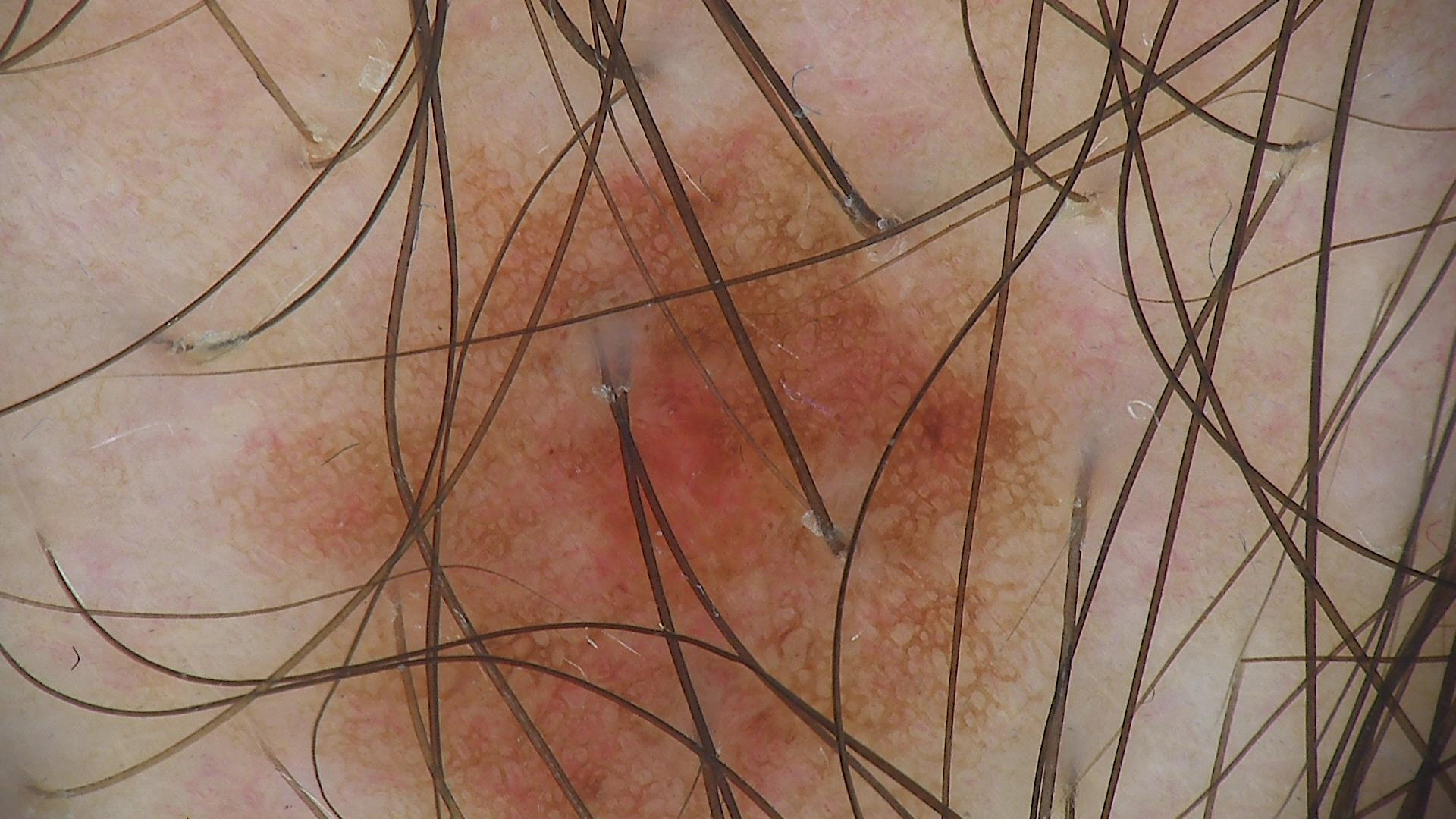Findings:
– diagnostic label — dysplastic junctional nevus (expert consensus)